Dermoscopy of a skin lesion. The patient says their skin tans without first burning. Referred with a clinical suspicion of basal cell carcinoma. A female patient aged 92. On a questionnaire the patient reported a personal history of cancer, a family history of skin cancer, no immunosuppression, and no prior organ transplant — 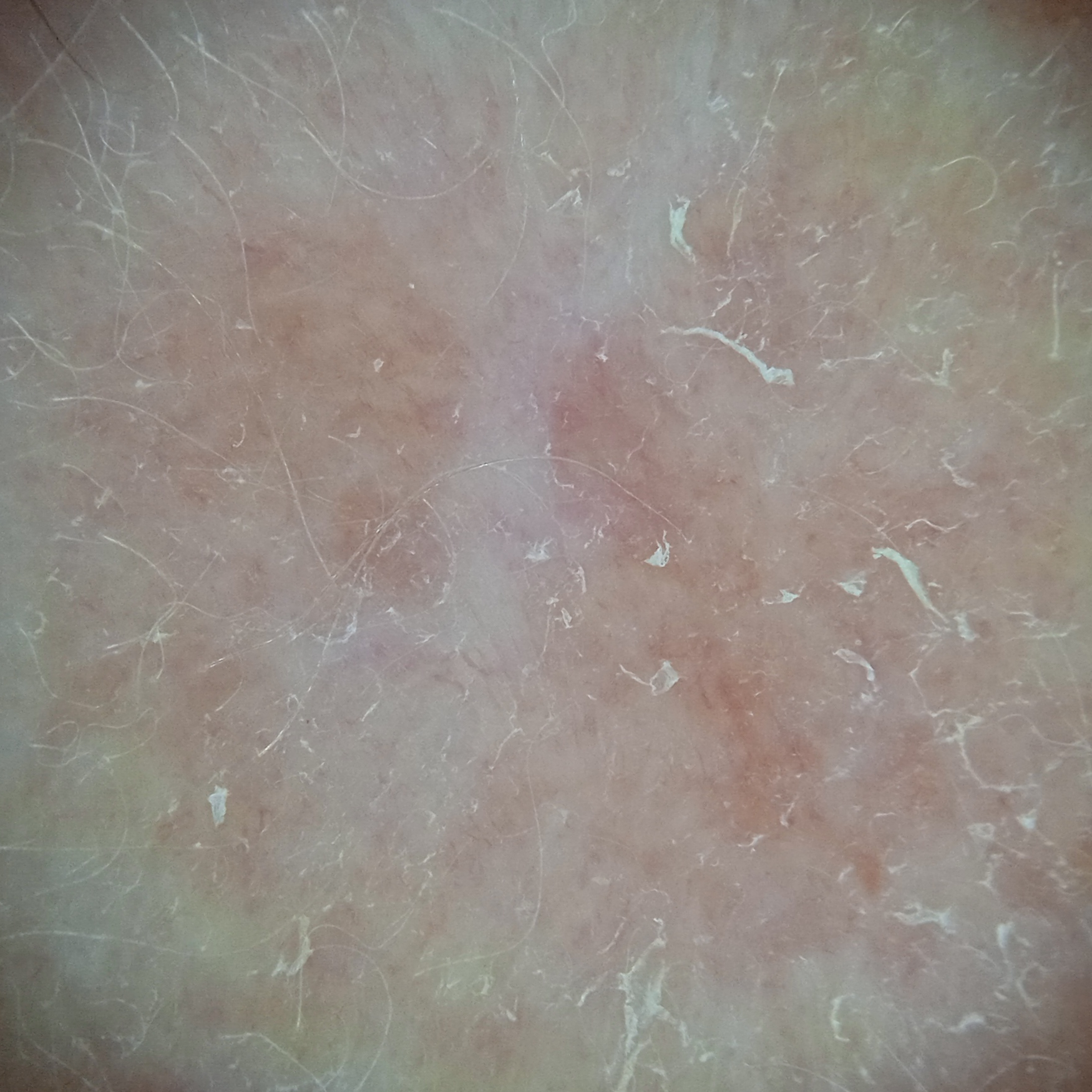- site: the face
- lesion size: 11.5 mm
- pathology: basal cell carcinoma (biopsy-proven)